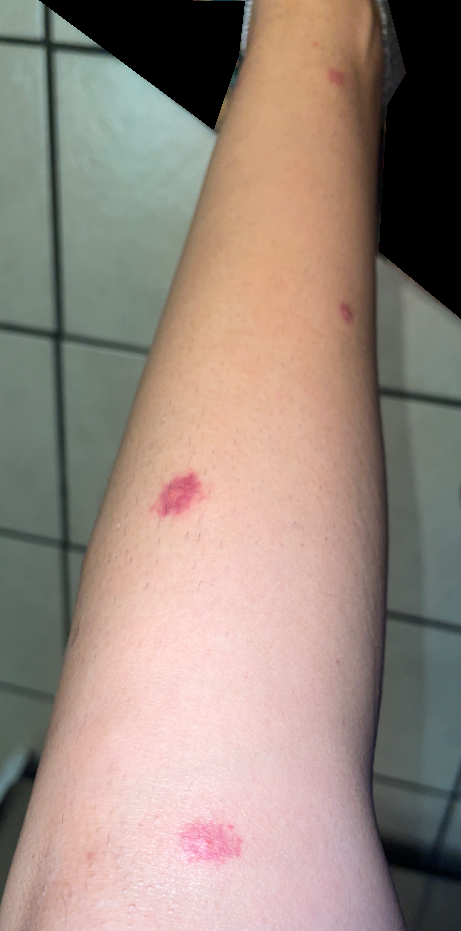assessment — the primary impression is Purpura; also raised was Insect Bite; lower on the differential is Benign cutaneous vascular tumor; less probable is Pigmented purpuric eruption